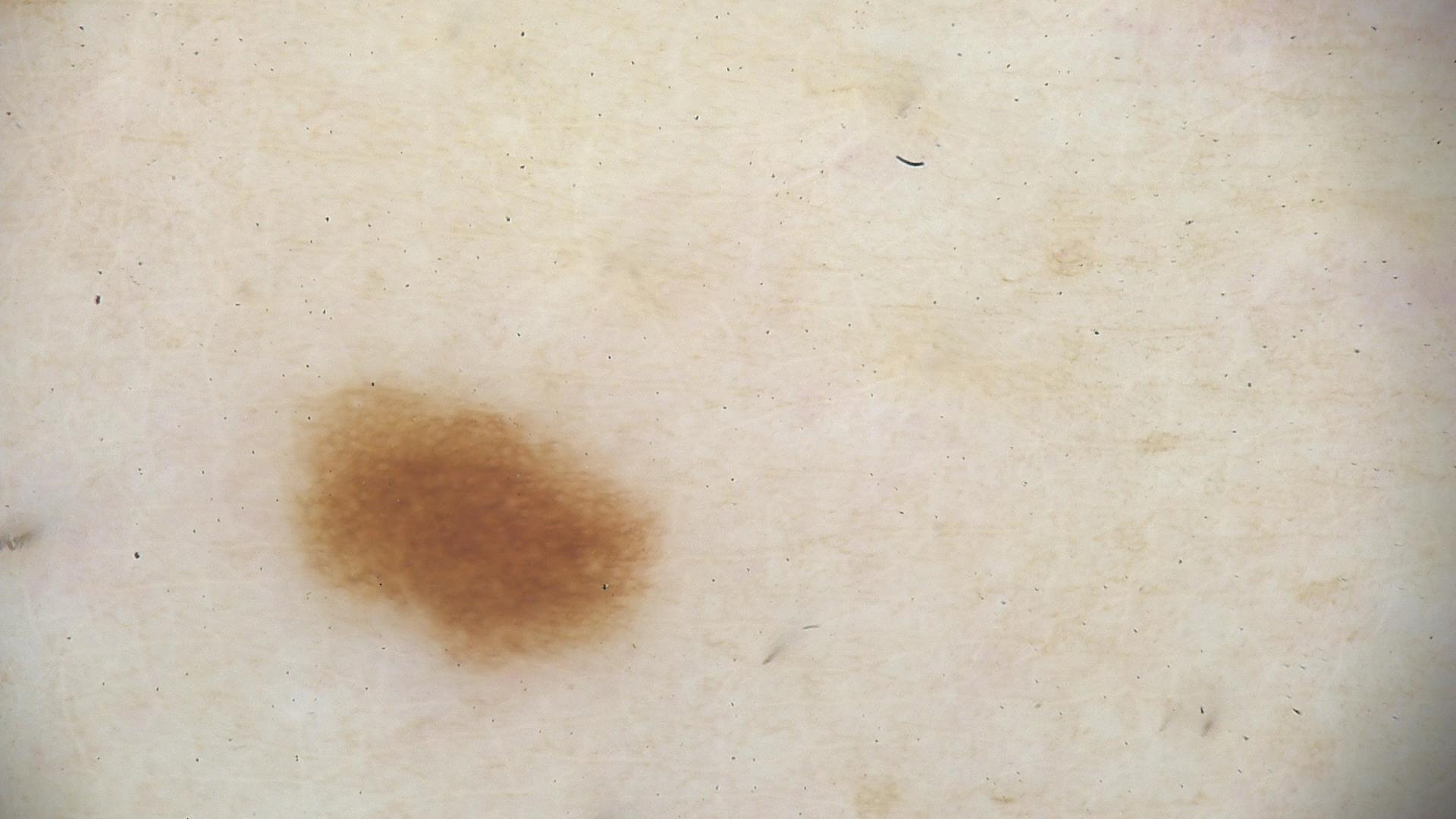A dermoscopic photograph of a skin lesion. The diagnosis was a benign lesion — a dysplastic junctional nevus.